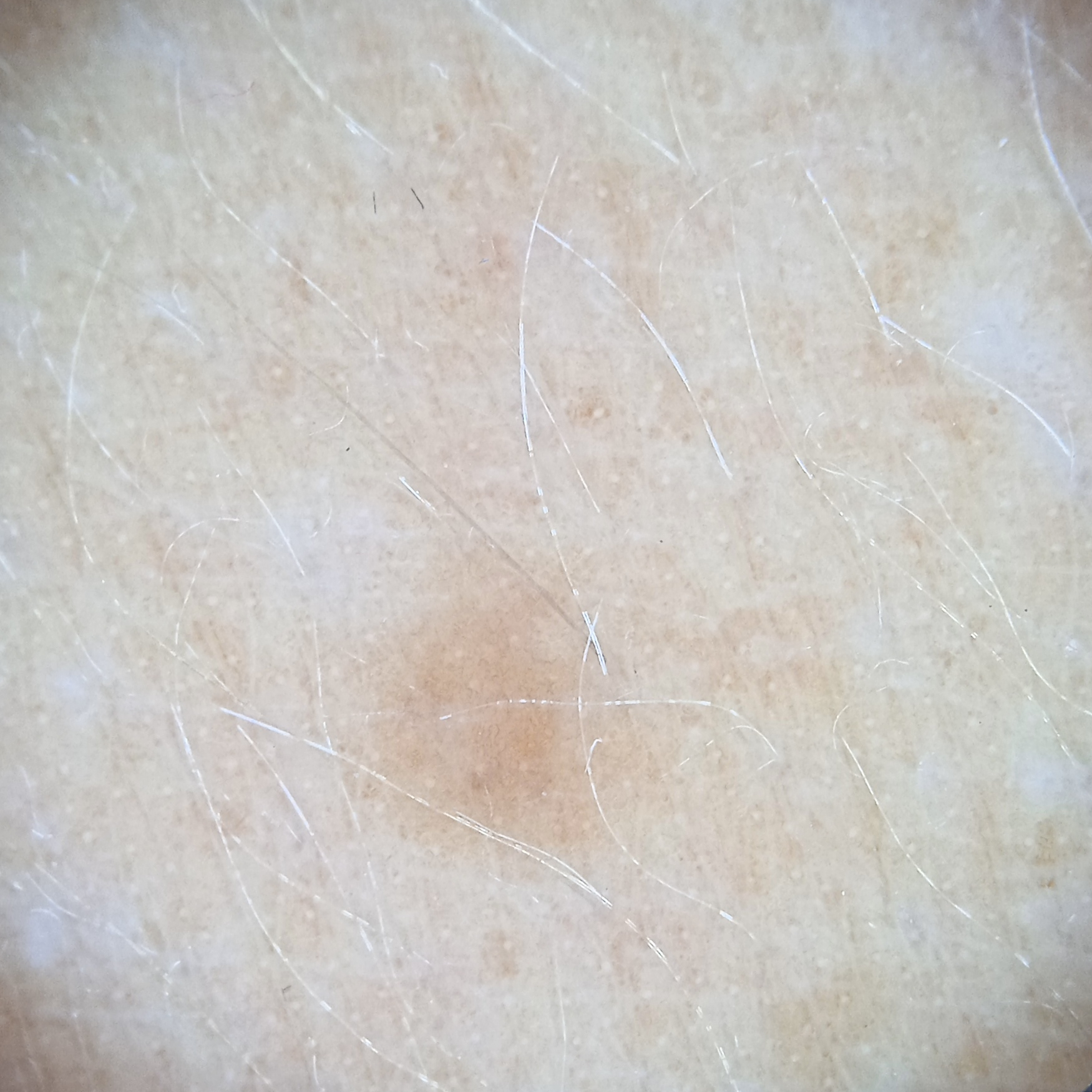The lesion was left diagnostically undetermined on review. Summary:
A dermoscopy image of a skin lesion. By self-report, a history of sunbed use. A female subject age 47. The patient says their skin tans without first burning. The lesion measures approximately 3.5 mm.